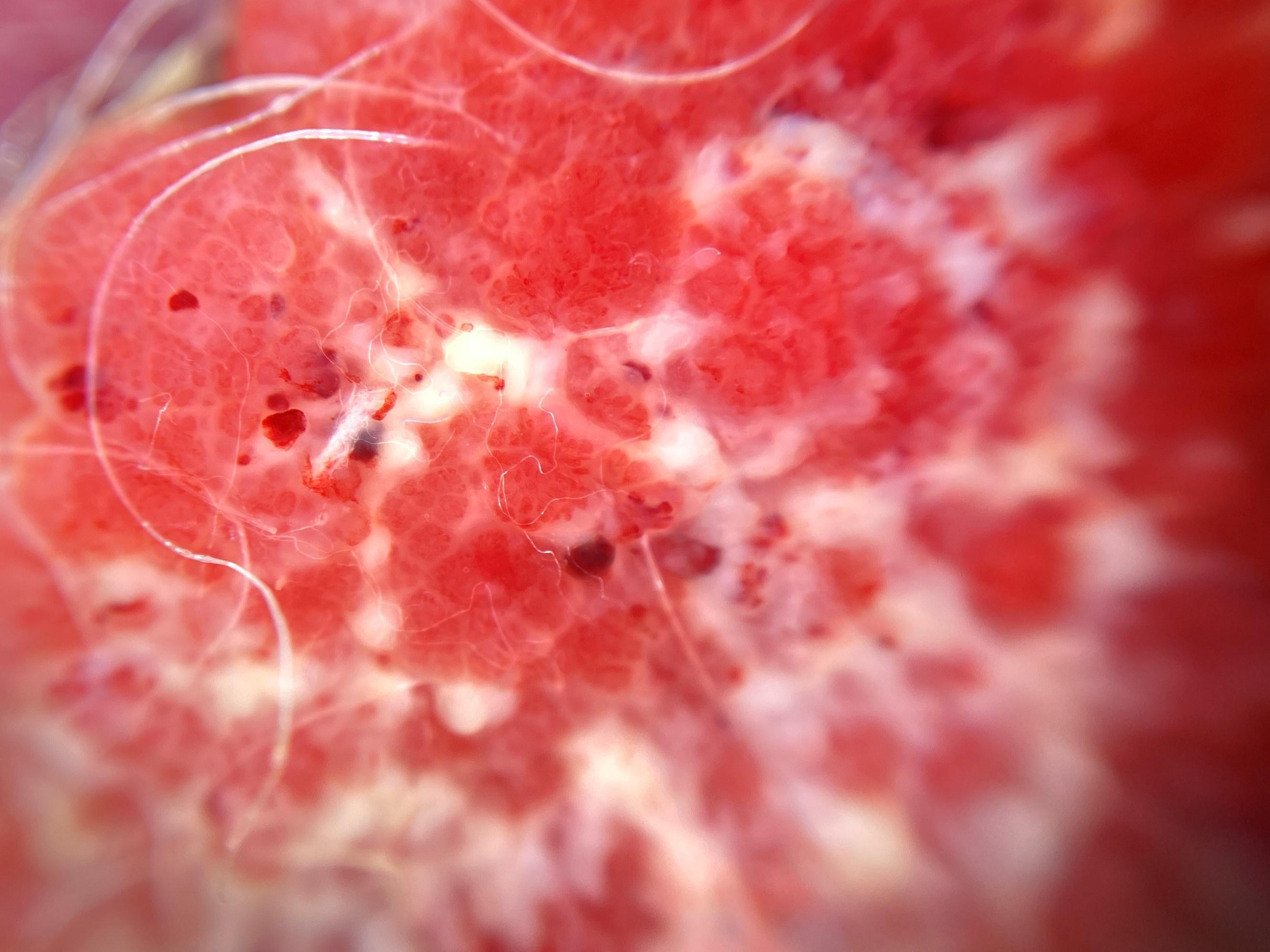  melanoma_history:
    personal_hx_melanoma: true
  patient:
    age_approx: 80
    sex: male
  skin_type: II
  image: dermoscopy
  lesion_location:
    region: the head or neck
  diagnosis:
    name: Squamous cell carcinoma
    malignancy: malignant
    confirmation: histopathology
    lineage: epidermal